The photograph is a close-up of the affected area:
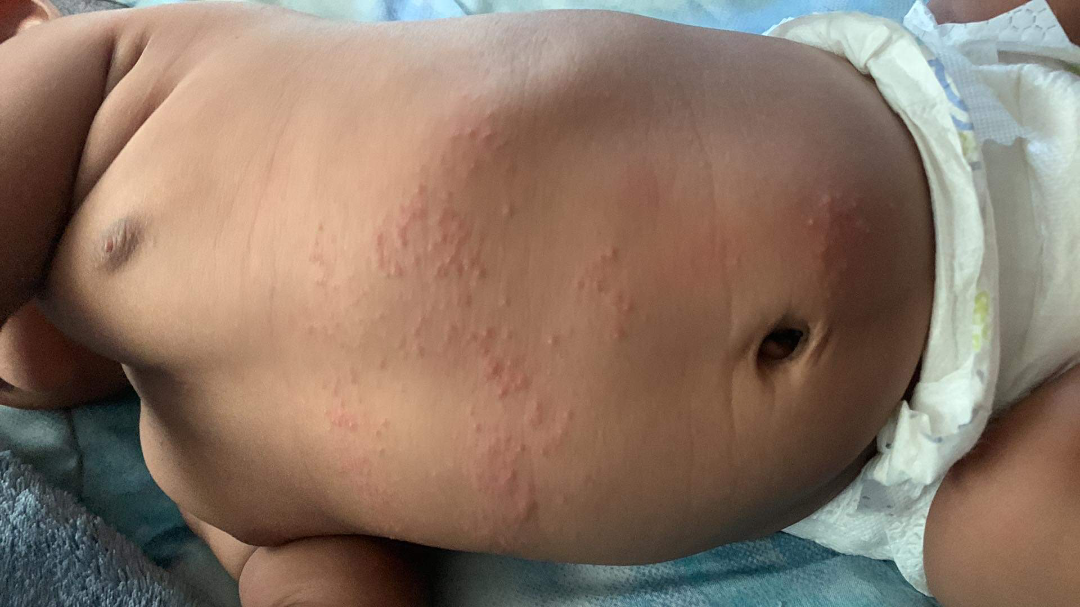assessment: could not be assessed.